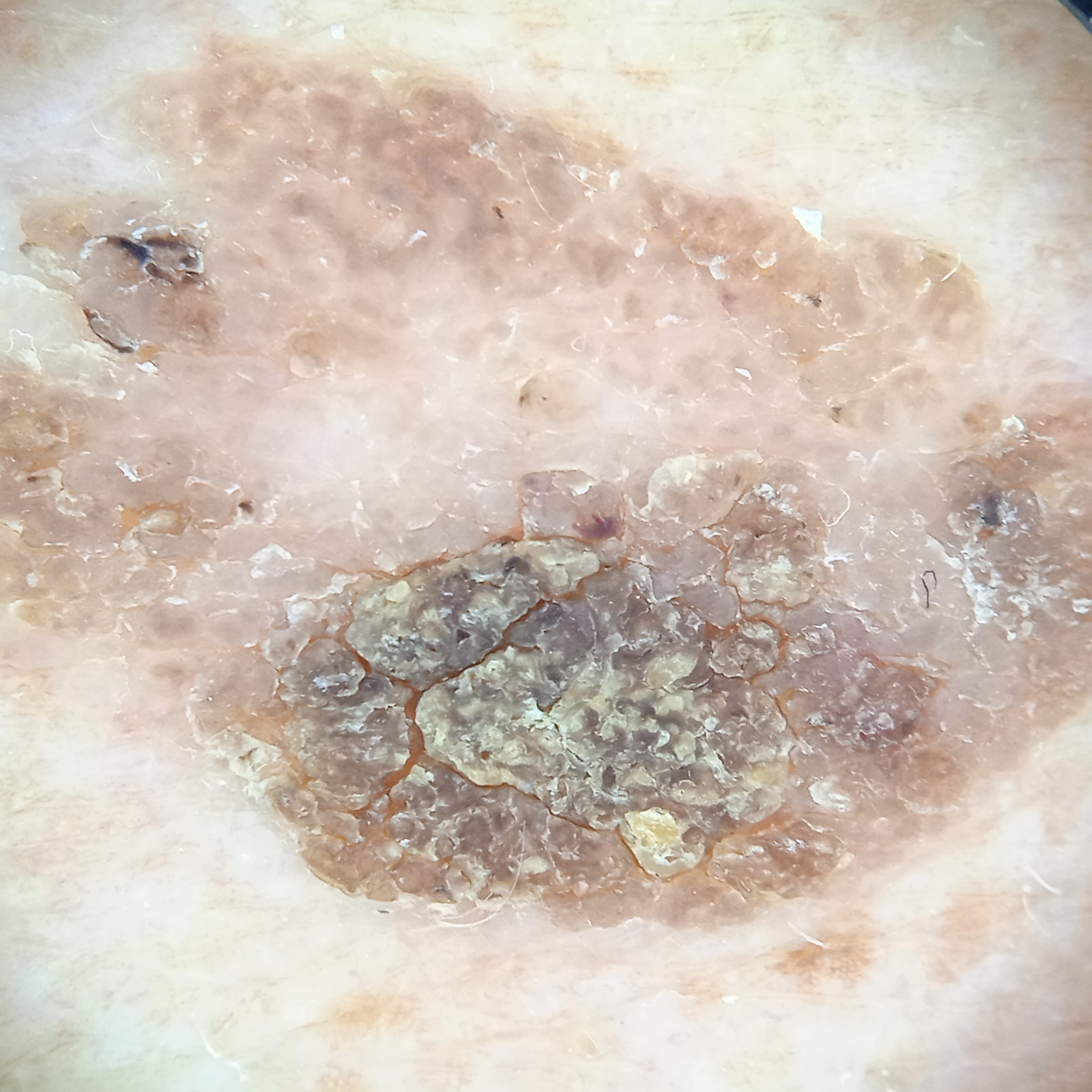Impression: The dermatologists' assessment was a seborrheic keratosis.